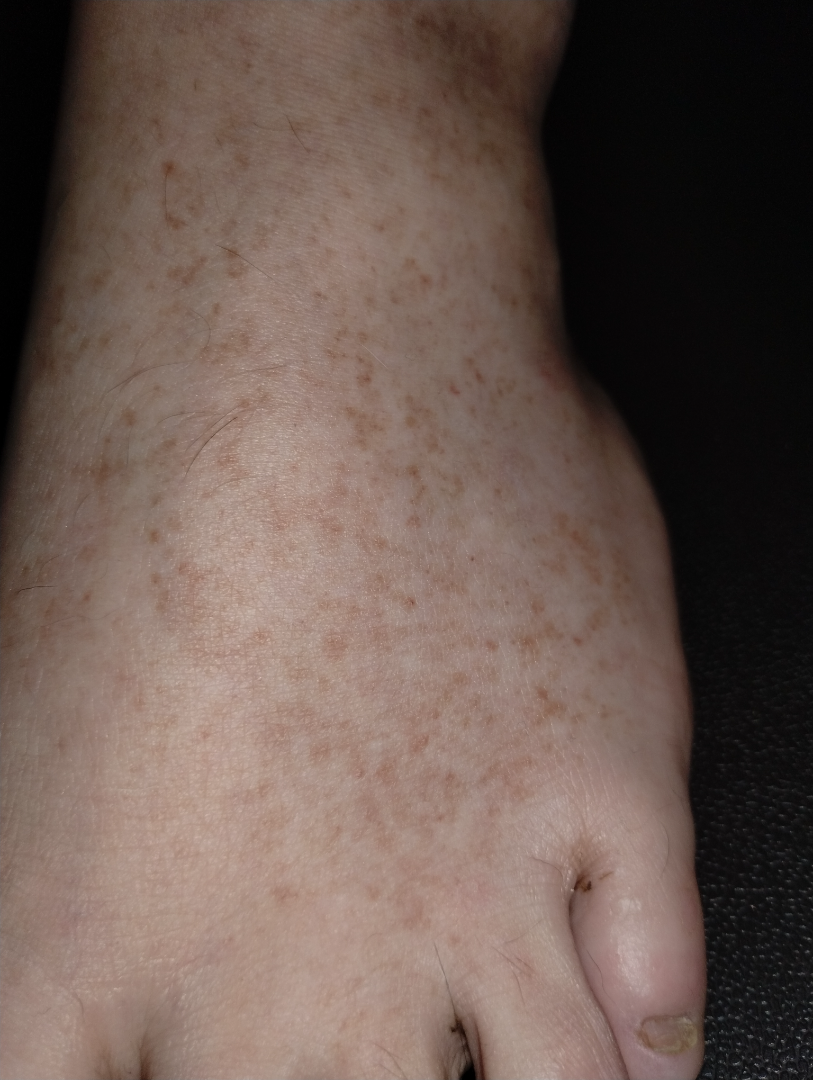Q: Patient demographics?
A: female, age 18–29
Q: Image view?
A: close-up
Q: What is the patient's skin tone?
A: self-reported Fitzpatrick IV; lay graders estimated Monk skin tone scale 2 or 3 (two reviewer pools)
Q: Duration?
A: one to three months
Q: Where on the body?
A: leg and top or side of the foot
Q: How does the lesion feel?
A: flat
Q: Reported symptoms?
A: bothersome appearance and enlargement
Q: Constitutional symptoms?
A: none reported
Q: How does the patient describe it?
A: a pigmentary problem
Q: What is the dermatologist's impression?
A: Hemosiderin pigmentation of lower limb due to varicose veins of lower limb (weight 0.67); Pigmented purpuric eruption (weight 0.33)